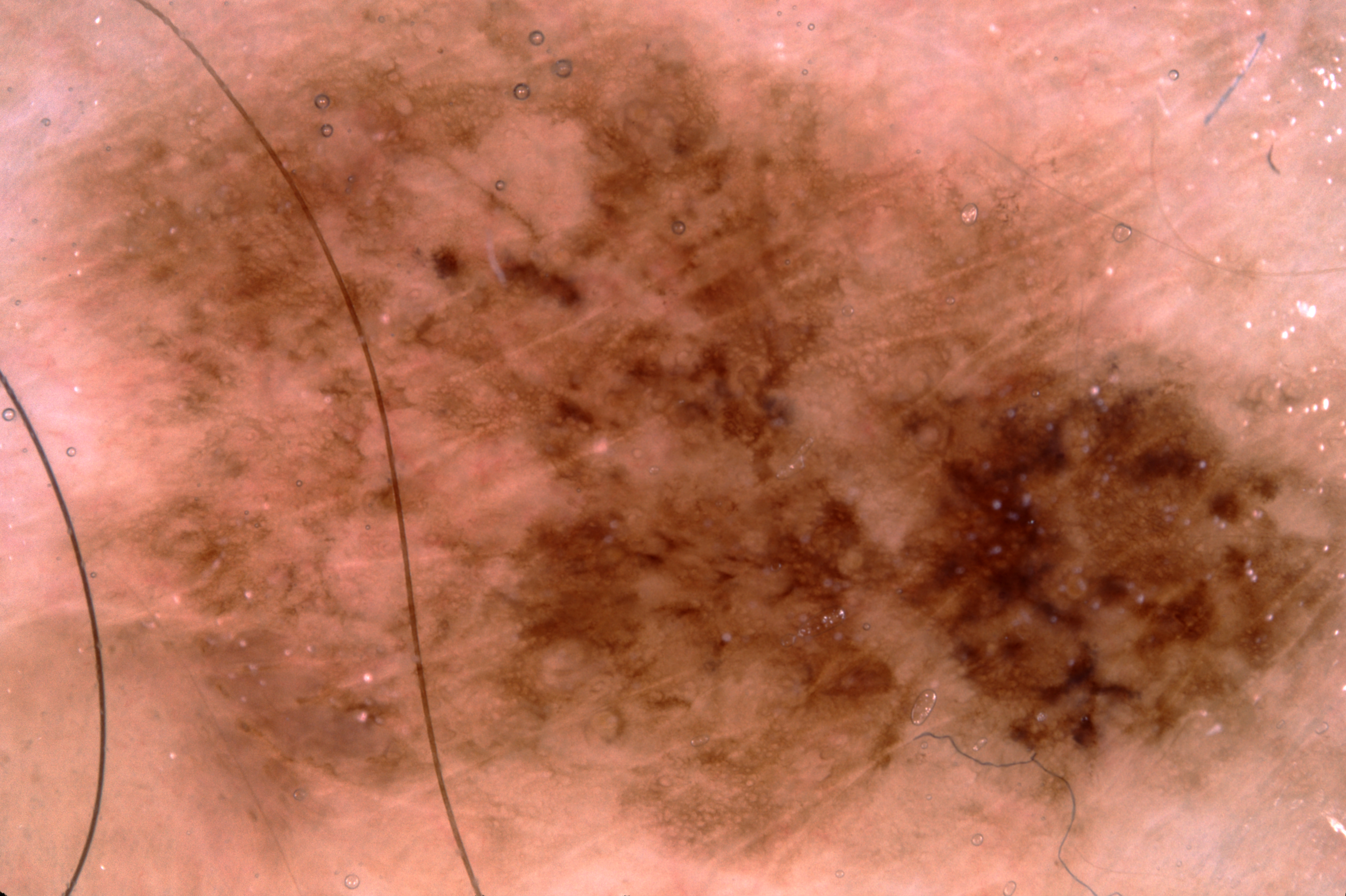subject=male, about 70 years old | image=dermoscopic image | features=pigment network and milia-like cysts; absent: negative network and streaks | field coverage=reaches across the whole image | diagnosis=a melanocytic nevus.